A female patient in their mid-20s. A dermoscopic view of a skin lesion.
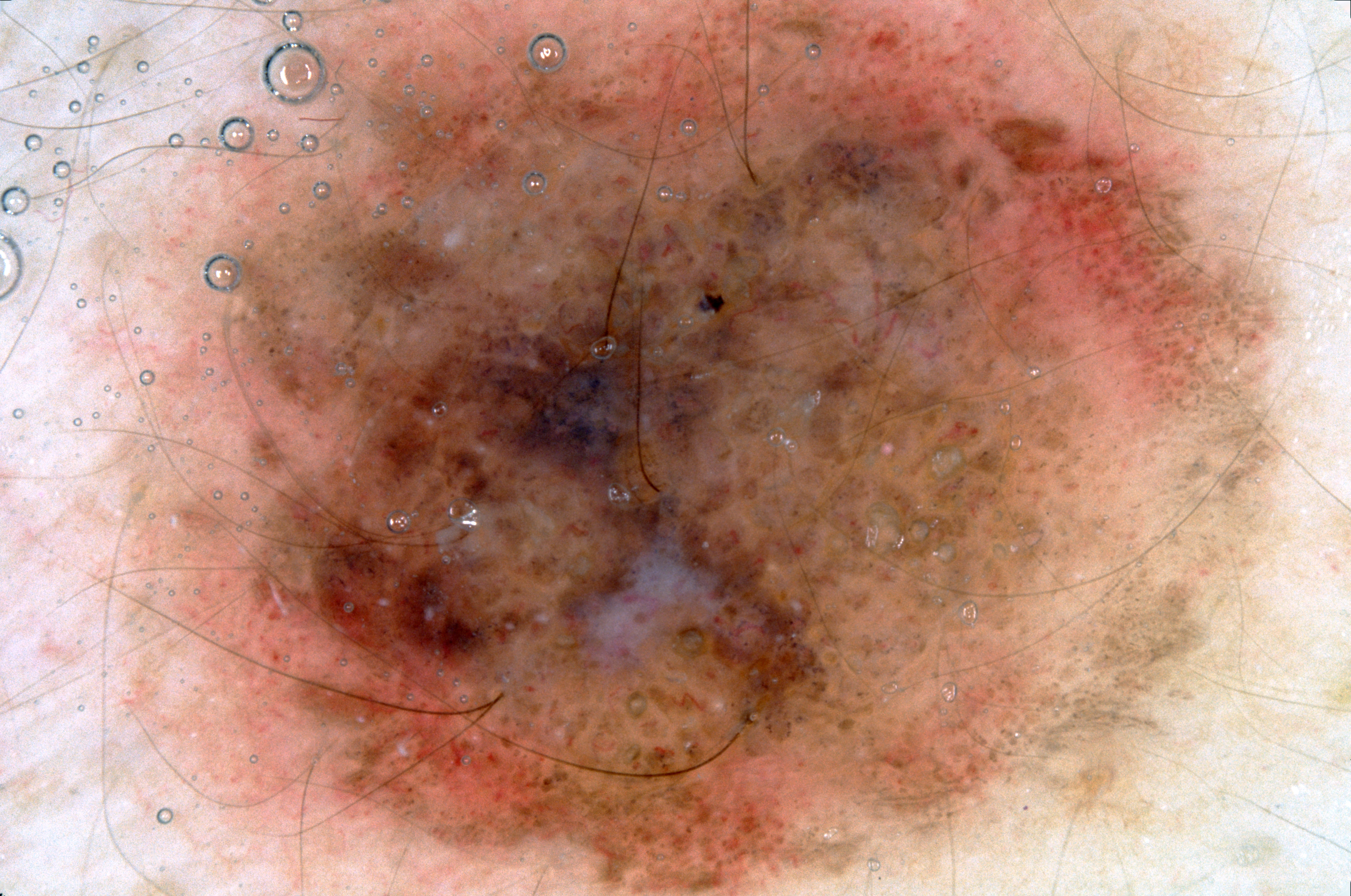dermoscopic pattern = negative network and milia-like cysts; absent: pigment network and streaks
size = ~75% of the field
lesion margin = extends past the field edge
lesion location = [116,0,1298,895]
assessment = a melanocytic nevus